A dermoscopic close-up of a skin lesion.
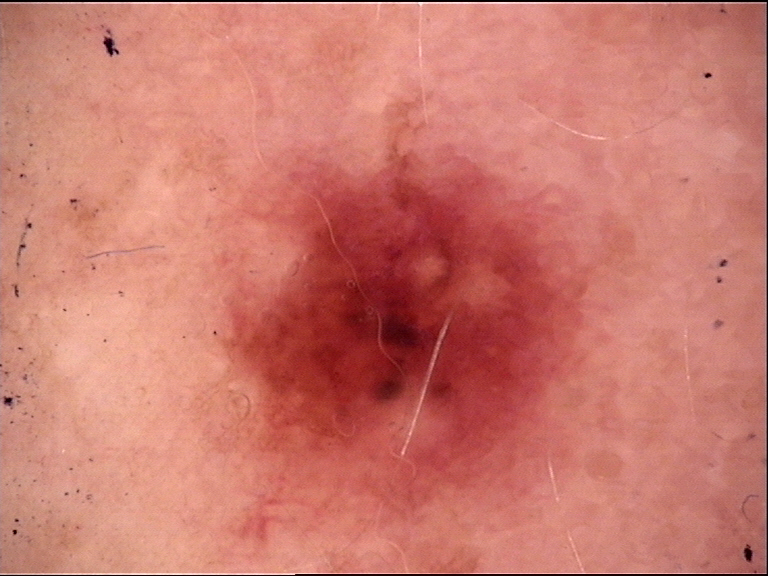Conclusion:
Consistent with a benign lesion — a dysplastic junctional nevus.